A skin lesion imaged with a dermatoscope.
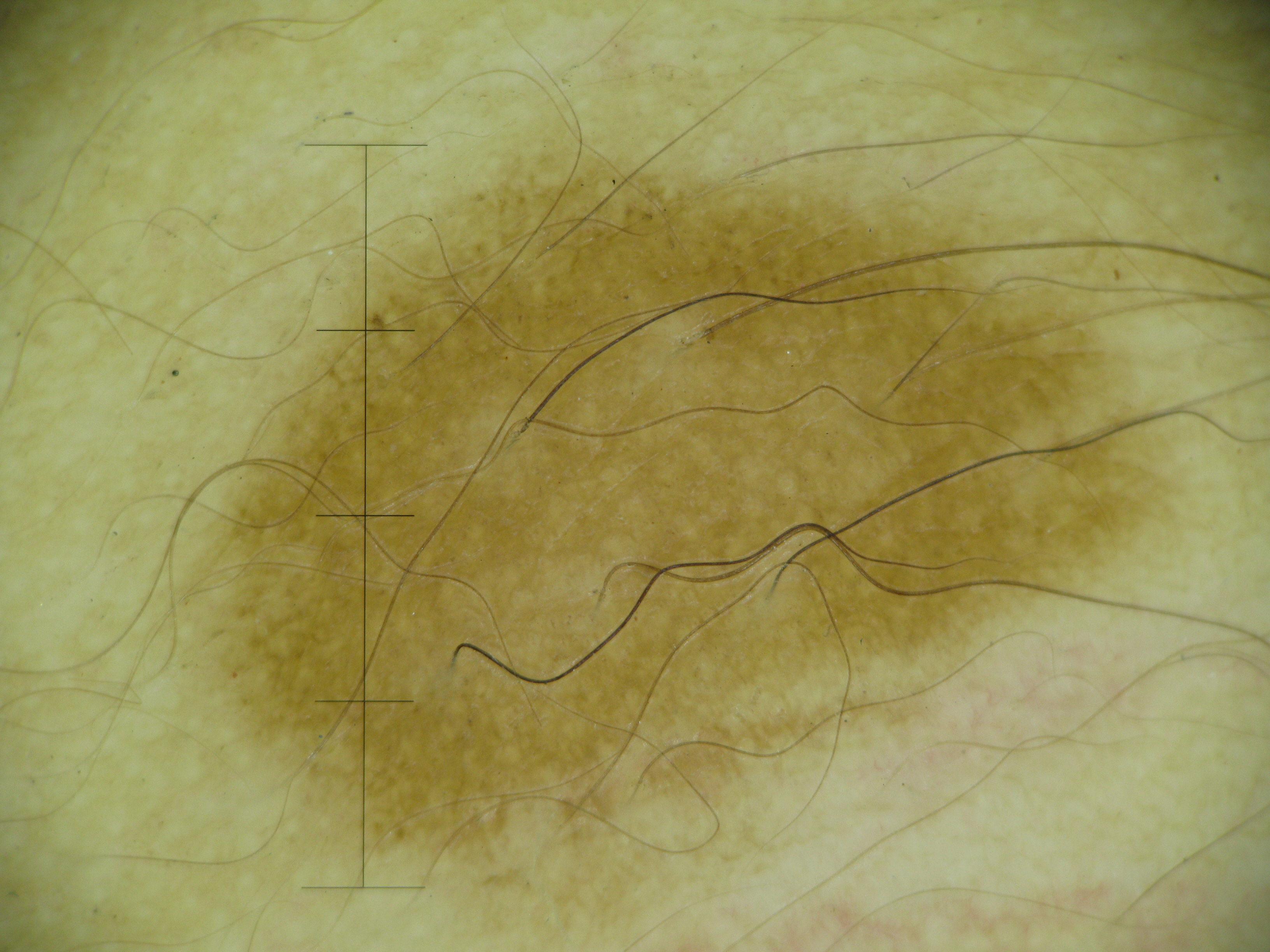Labeled as a banal lesion — a junctional nevus.